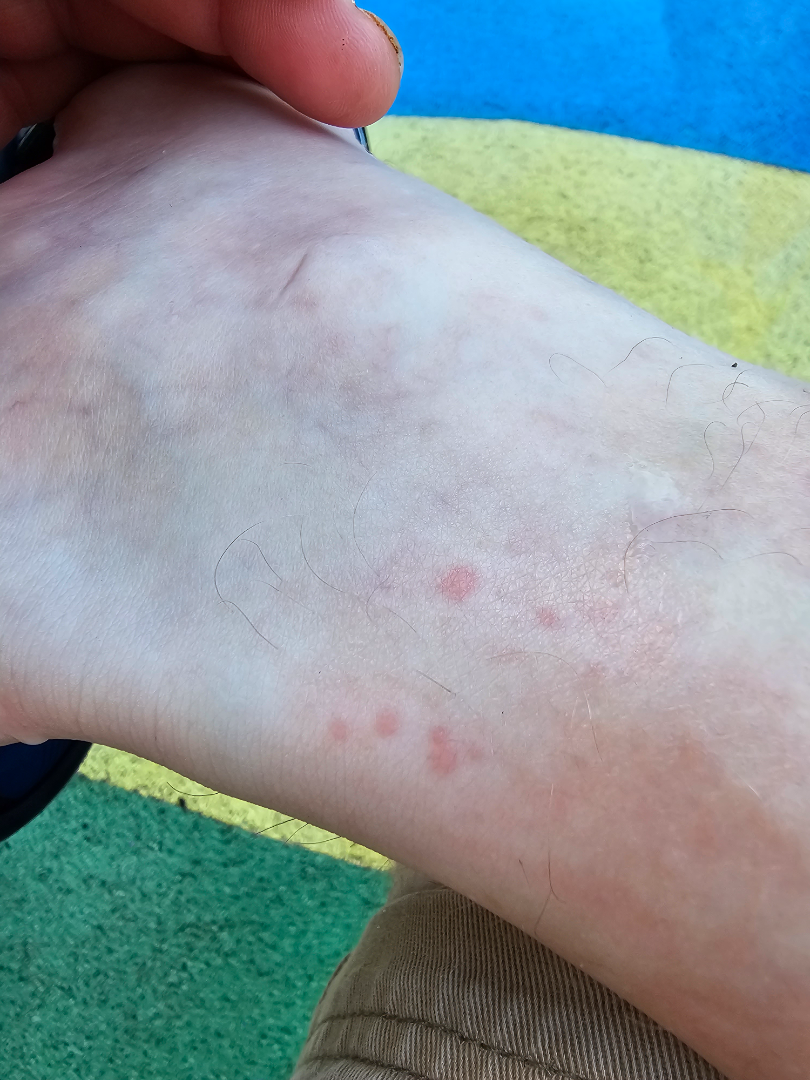The reviewing dermatologist was unable to assign a differential diagnosis from the image.